This is a close-up image.
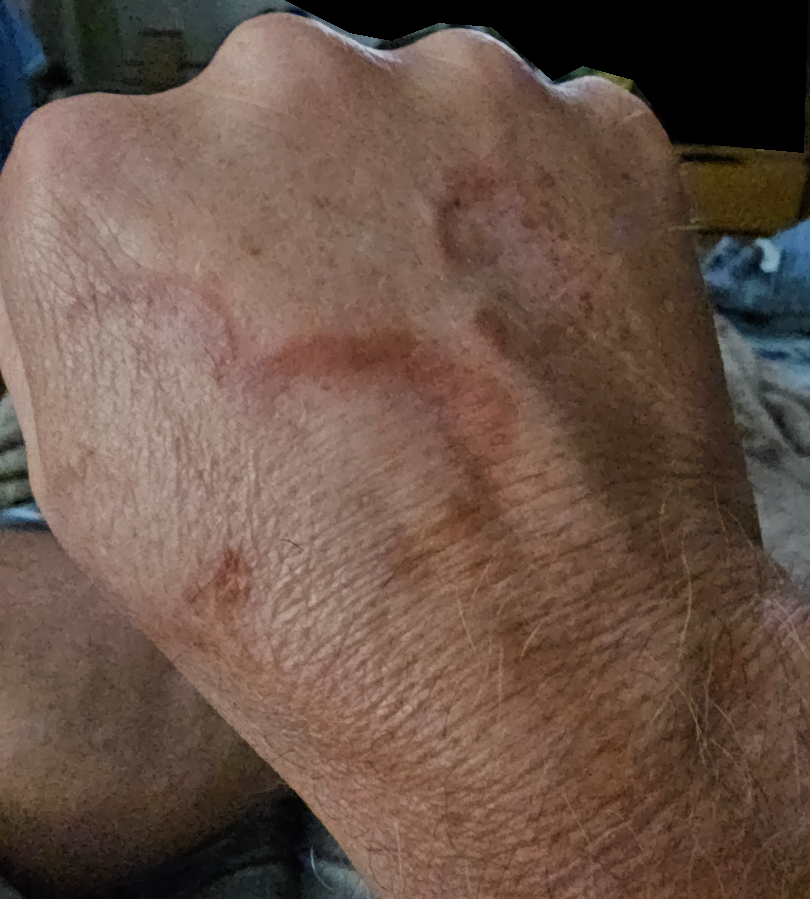Review:
Consistent with Granuloma annulare.